A dermatoscopic image of a skin lesion.
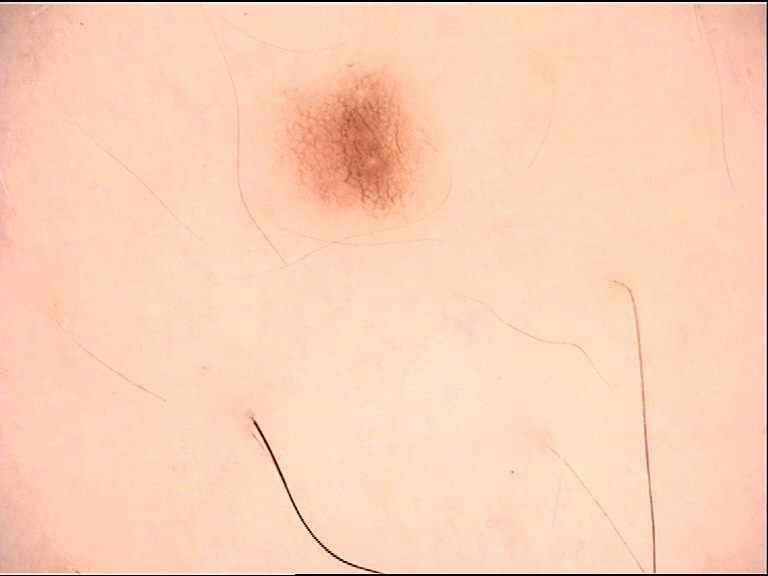Labeled as a dysplastic junctional nevus.